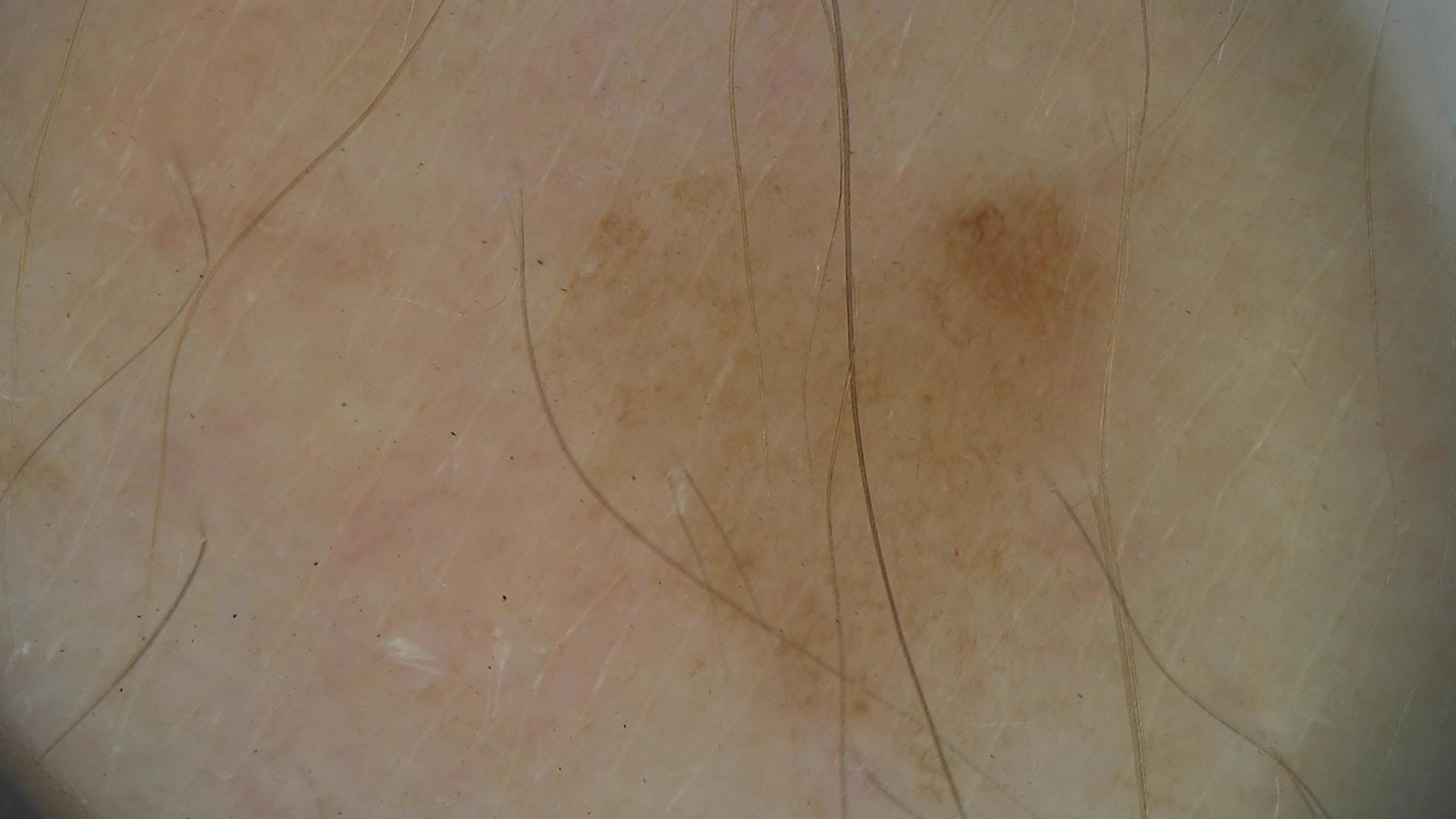A dermoscopy image of a single skin lesion.
Consistent with a benign lesion — a dysplastic junctional nevus.